The patient is a female aged 18–29, the photo was captured at a distance, the affected area is the back of the hand: 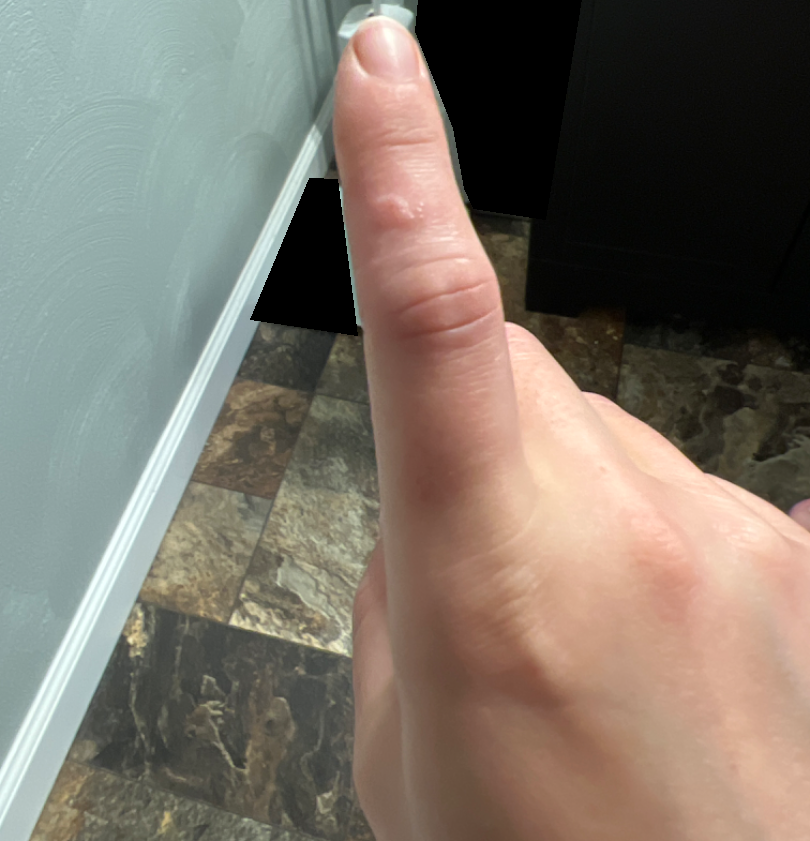Diagnostic features were not clearly distinguishable in this photograph.